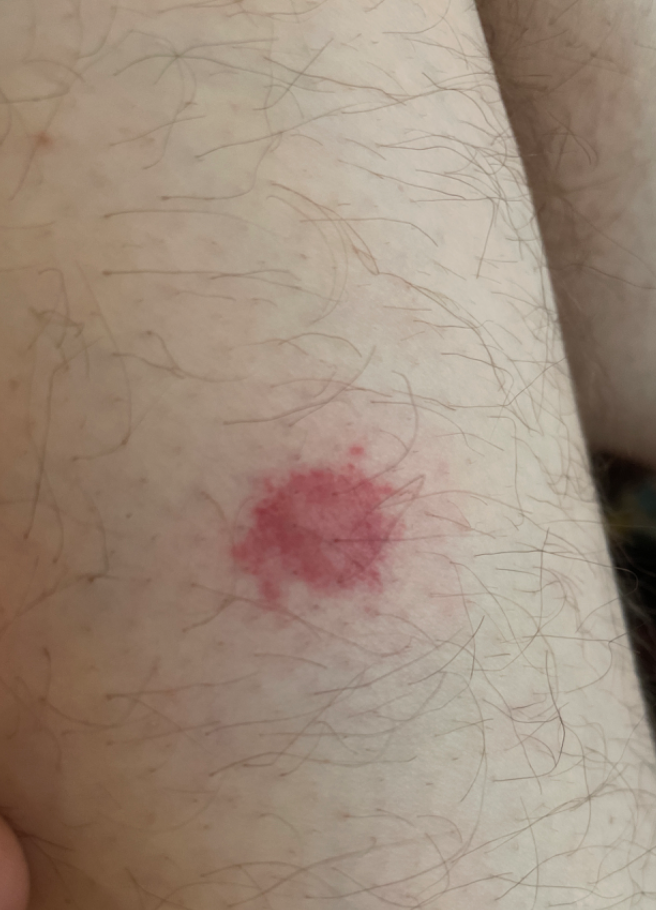  texture: raised or bumpy
  patient_category: a rash
  systemic_symptoms: none reported
  patient: male, age 30–39
  symptoms:
    - bothersome appearance
    - itching
  duration: less than one week
  shot_type: close-up
  body_site: leg
  differential:
    tied_lead:
      - Purpura
      - ecchymoses
    unlikely:
      - Pigmented purpuric eruption
      - Insect Bite
      - Hemangioma